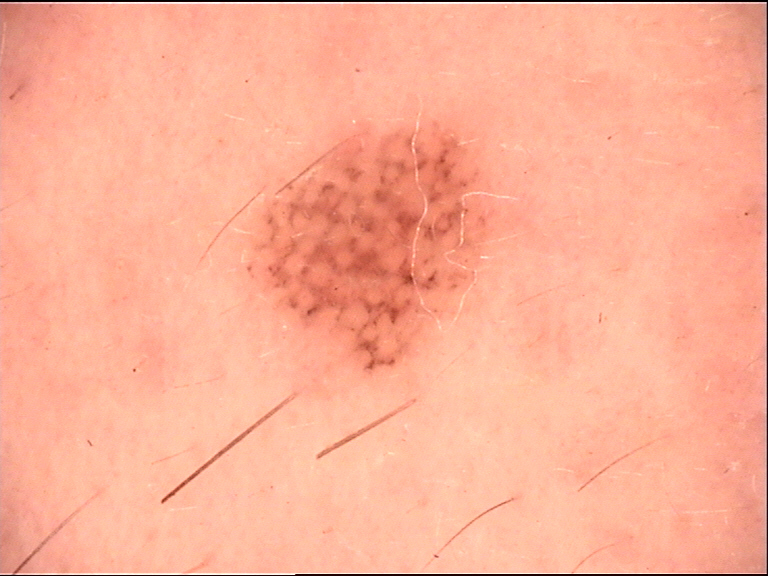imaging = dermoscopy
class = Miescher nevus (expert consensus)